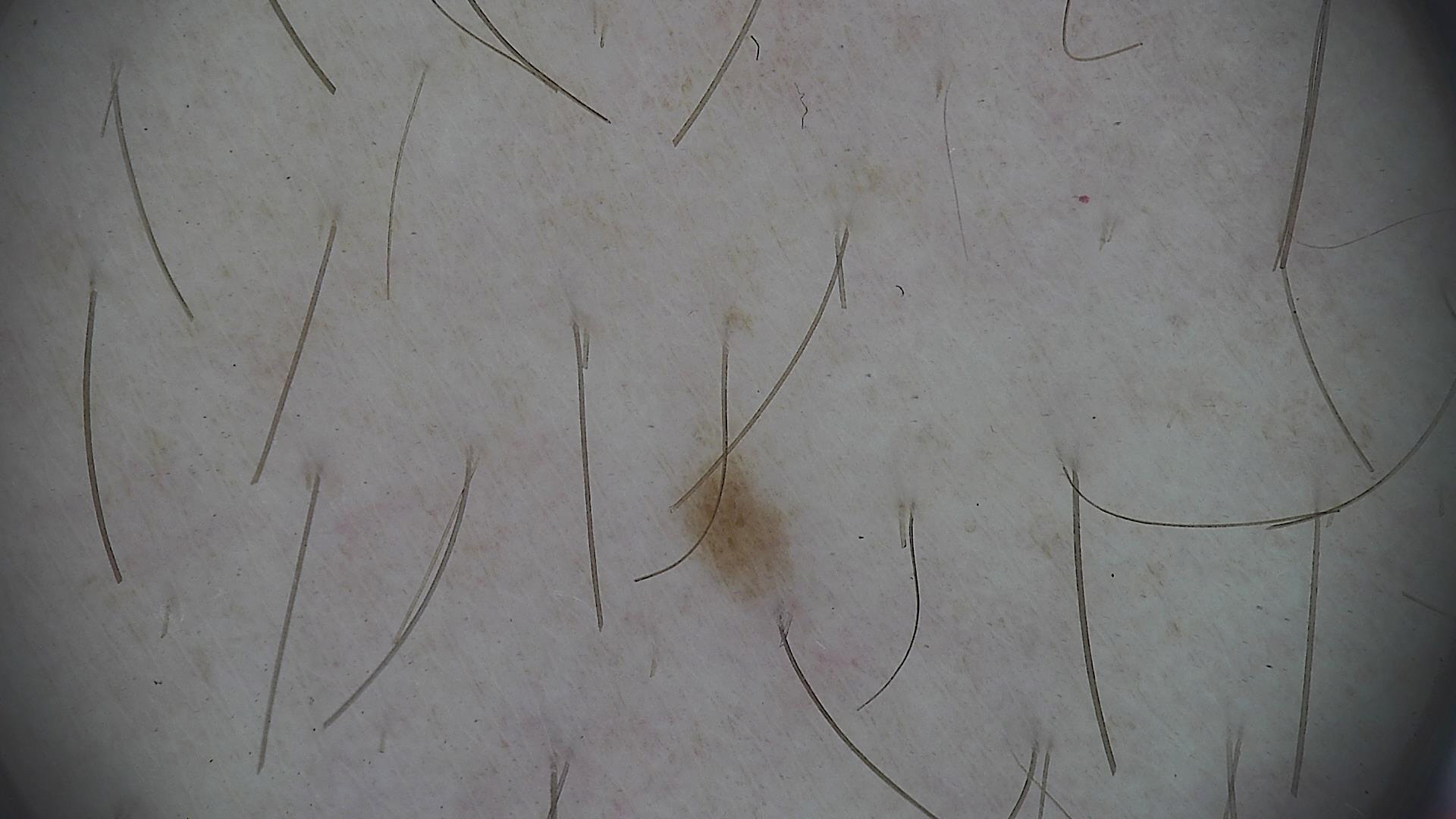A skin lesion imaged with a dermatoscope.
The diagnostic label was a junctional nevus.